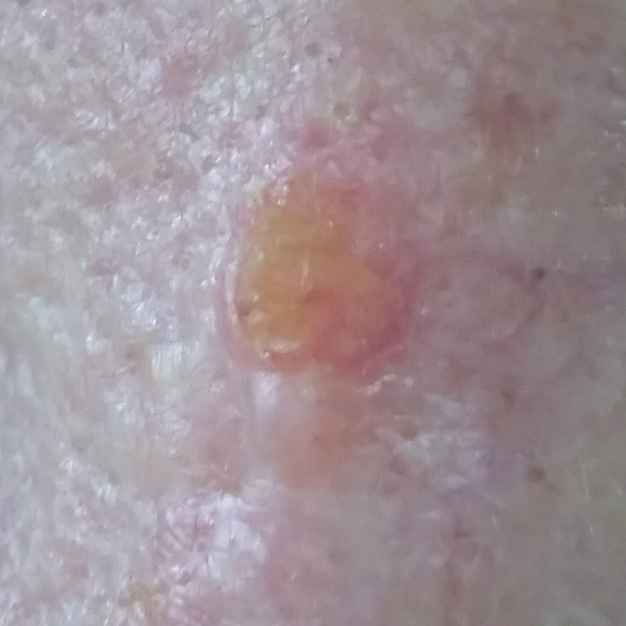By history, prior skin cancer (patient or family).
A female subject age 62.
A clinical close-up photograph of a skin lesion.
Recorded as Fitzpatrick phototype II.
The lesion is located on the nose.
Histopathological examination showed a squamous cell carcinoma.